An image taken at a distance; located on the arm; the contributor is 18–29, female.
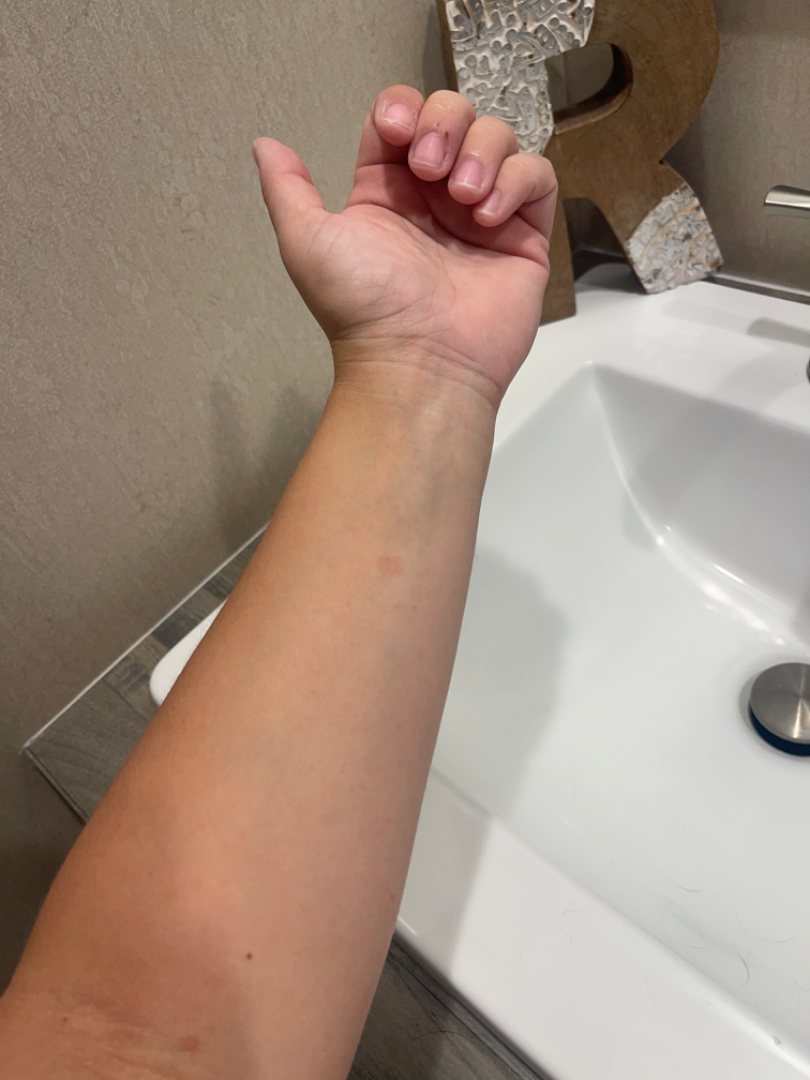Impression: The reviewing dermatologist was unable to assign a differential diagnosis from the image. History: The condition has been present for one to four weeks. No constitutional symptoms were reported. Texture is reported as flat. No associated lesion symptoms were reported.